A skin lesion imaged with a dermatoscope: 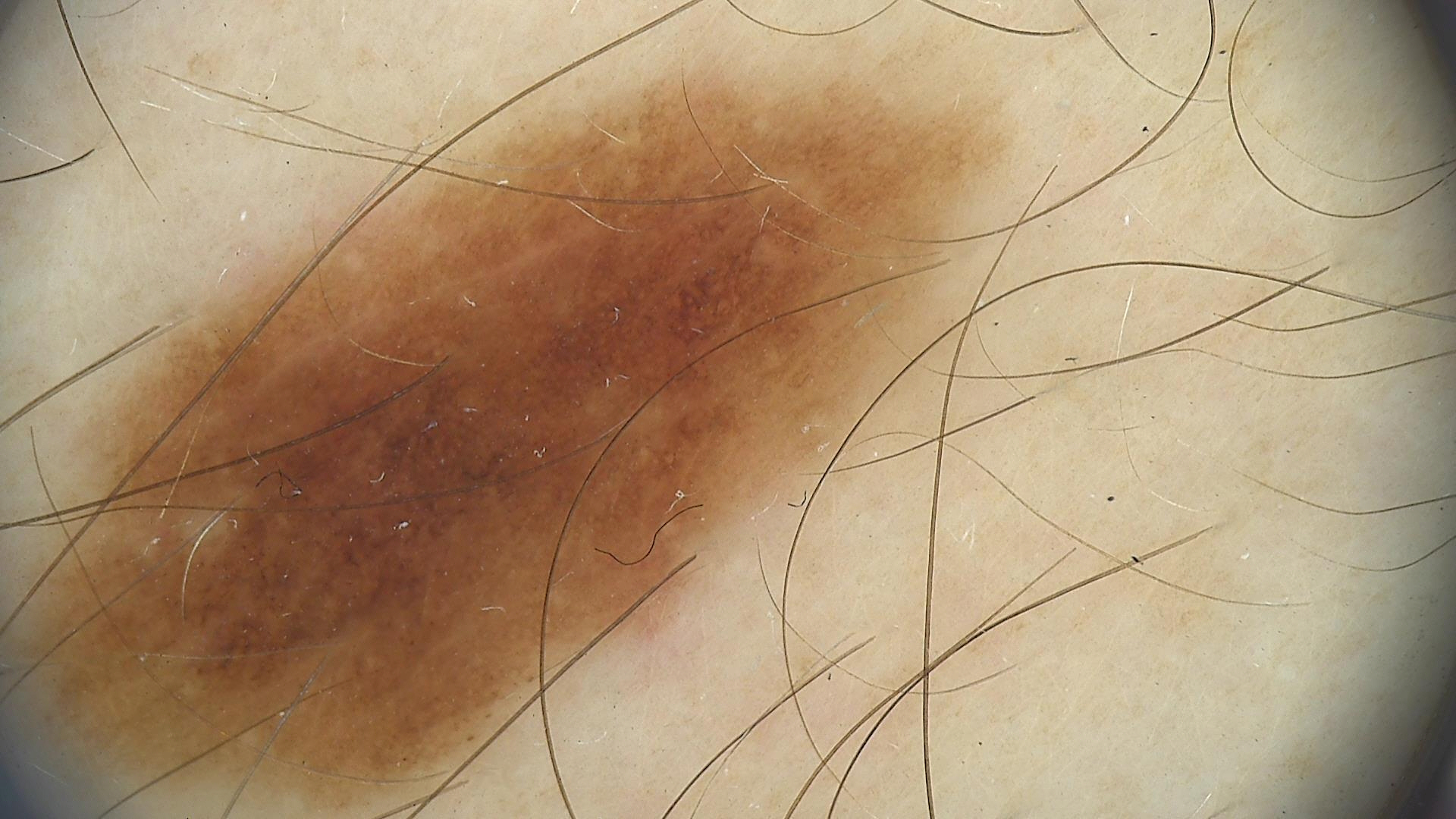Classified as a benign lesion — a dysplastic junctional nevus.